The photograph is a close-up of the affected area — 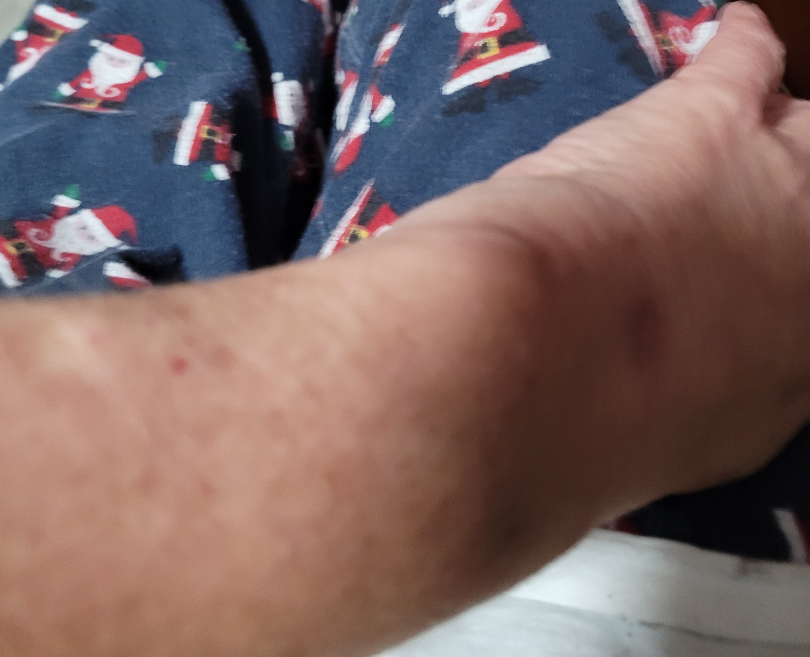The skin condition could not be confidently assessed from this image.